This image was taken at a distance. Symptoms reported: burning, itching, pain and bothersome appearance. The affected area is the head or neck, leg and top or side of the foot. The patient considered this a rash. The patient reports the lesion is raised or bumpy and fluid-filled. Present for less than one week:
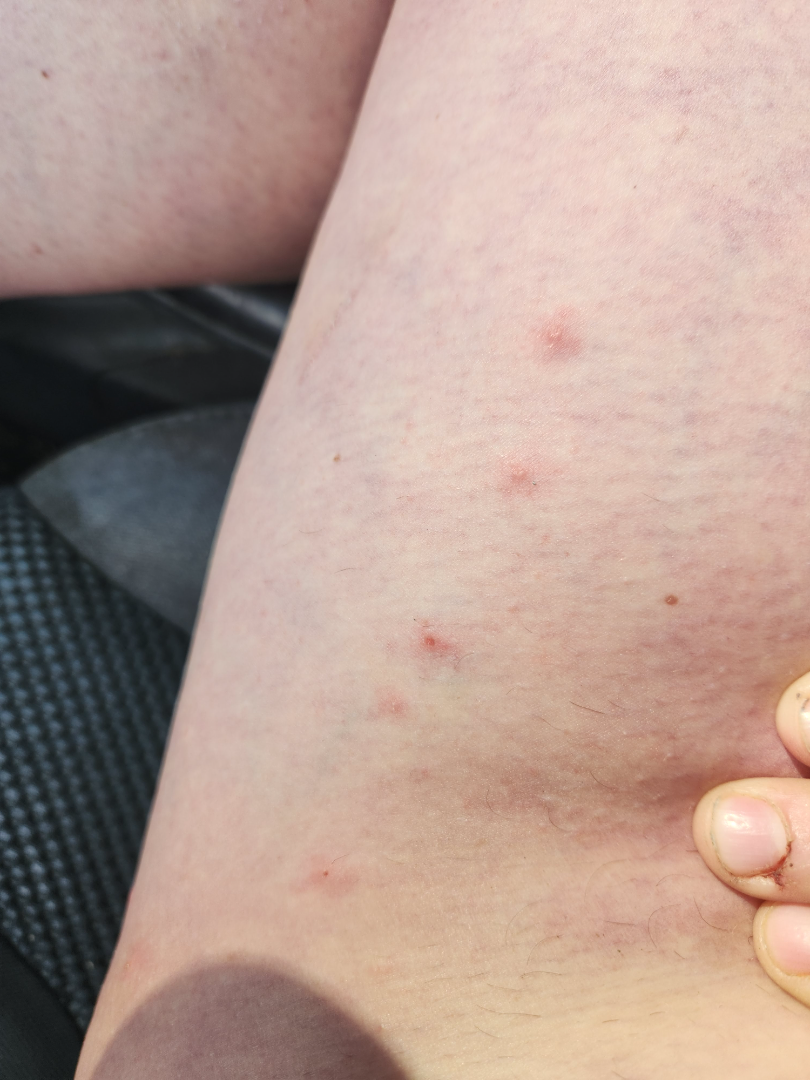Diagnostic features were not clearly distinguishable in this photograph.